A dermoscopic image of a skin lesion: 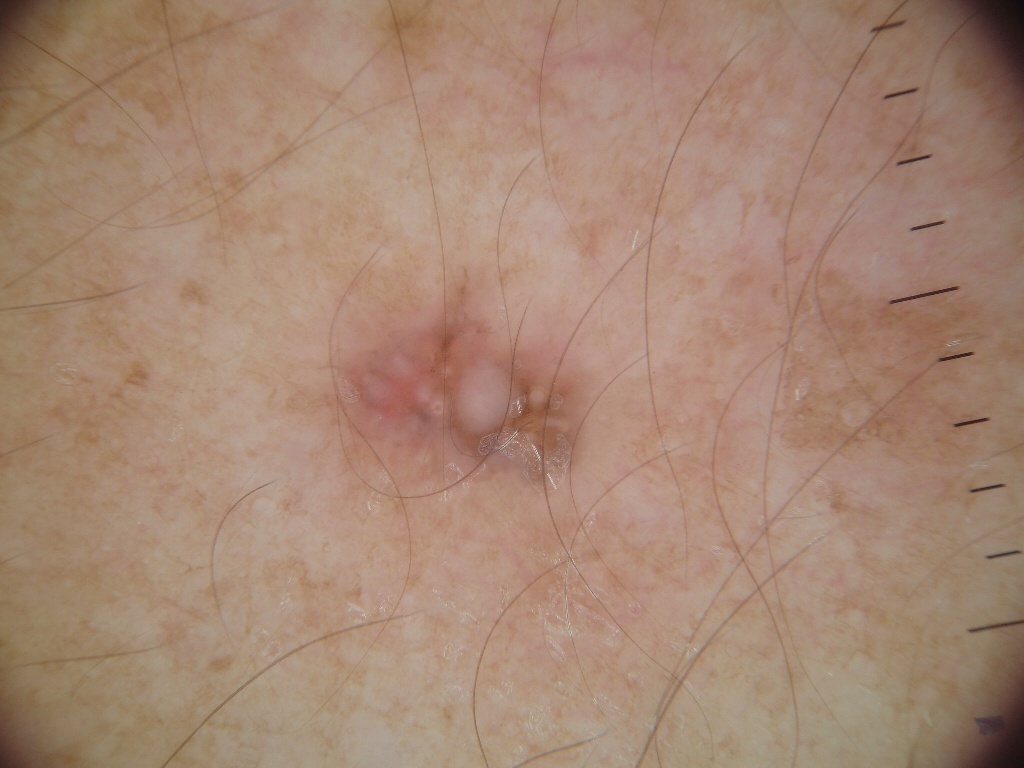Notes:
– lesion location · 296/269/620/506
– extent · ~8% of the field
– dermoscopic features not present · globules and streaks
– impression · a skin cancer